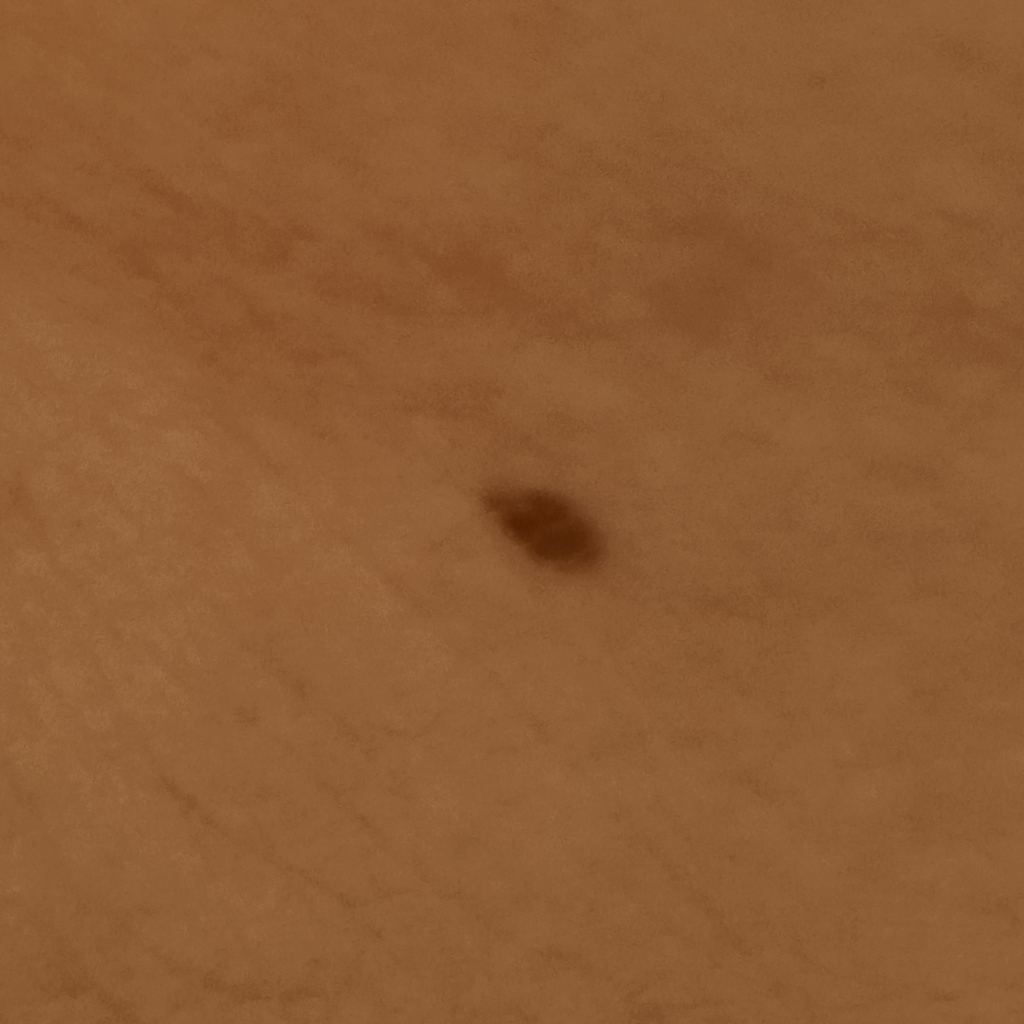* relevant history · a personal history of skin cancer, a personal history of cancer, no prior organ transplant
* clinical context · research study (no referral diagnosis)
* subject · female, age 60
* nevus count · few melanocytic nevi overall
* sun reaction · skin tans without first burning
* site · the torso
* lesion size · 6.2 mm
* diagnostic label · seborrheic keratosis (dermatologist consensus)